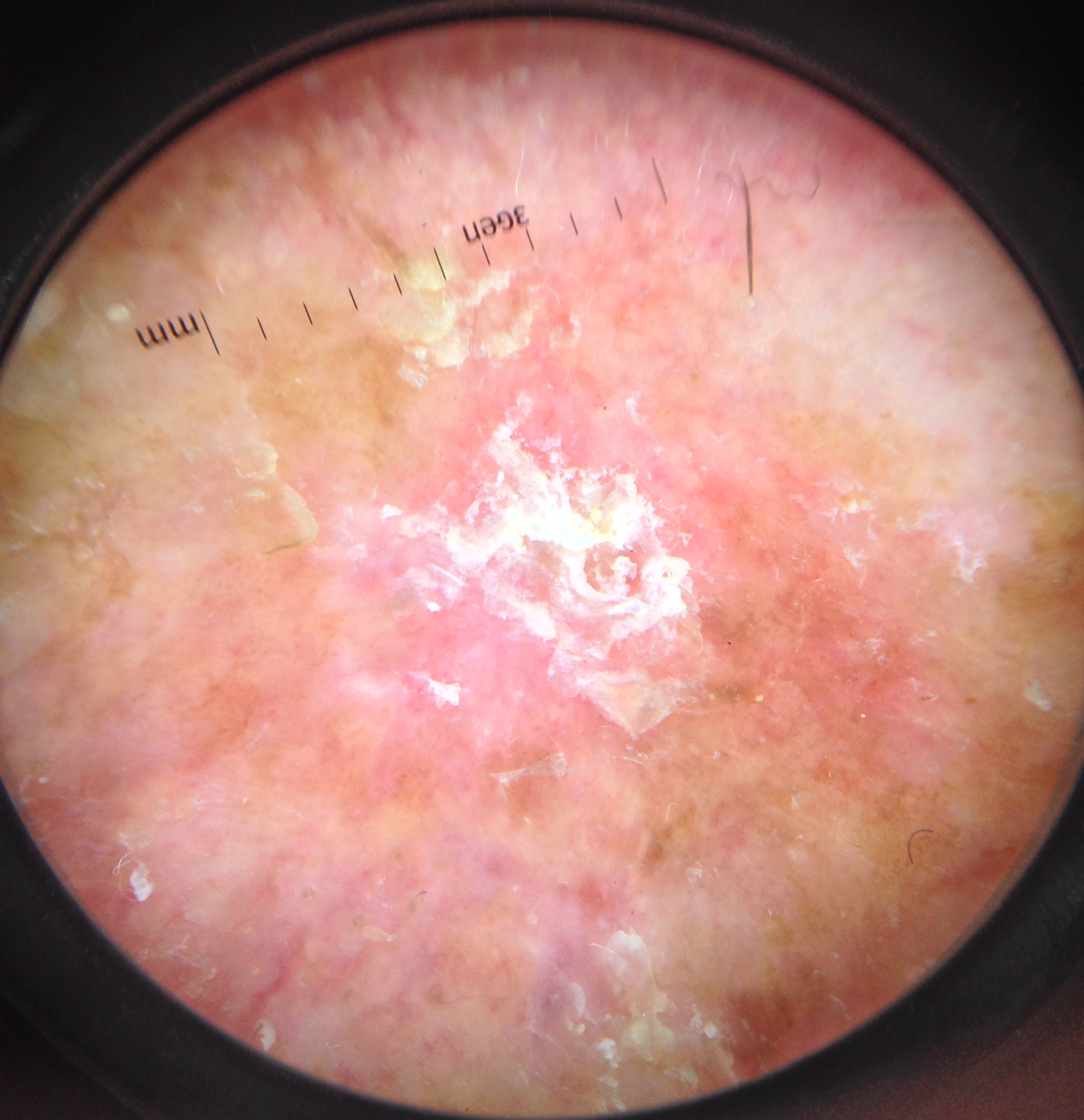A dermatoscopic image of a skin lesion.
Histopathology confirmed a keratinocytic, malignant lesion — a squamous cell carcinoma.